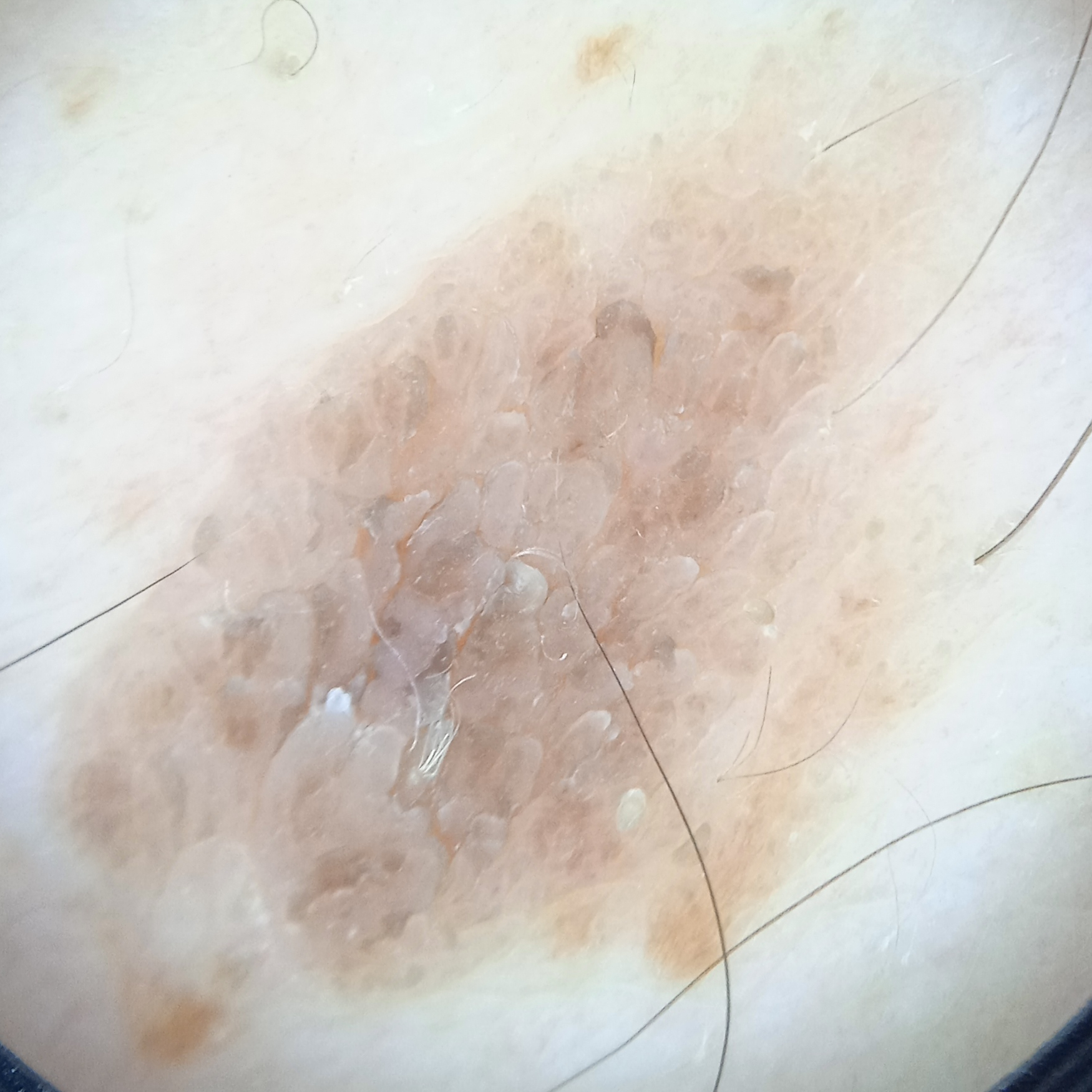diagnostic label: seborrheic keratosis (dermatologist consensus).